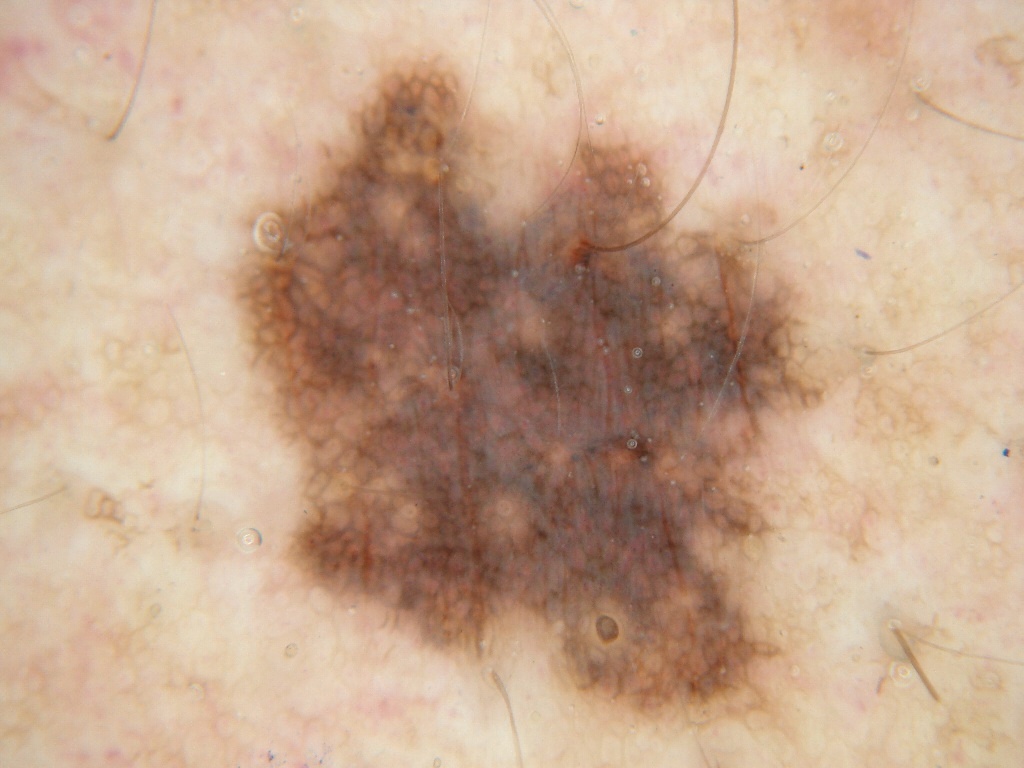The patient is a male aged around 50.
A skin lesion imaged with a dermatoscope.
The lesion is bounded by 230 63 826 726.
Dermoscopically, the lesion shows pigment network.
Clinically diagnosed as a melanocytic nevus.